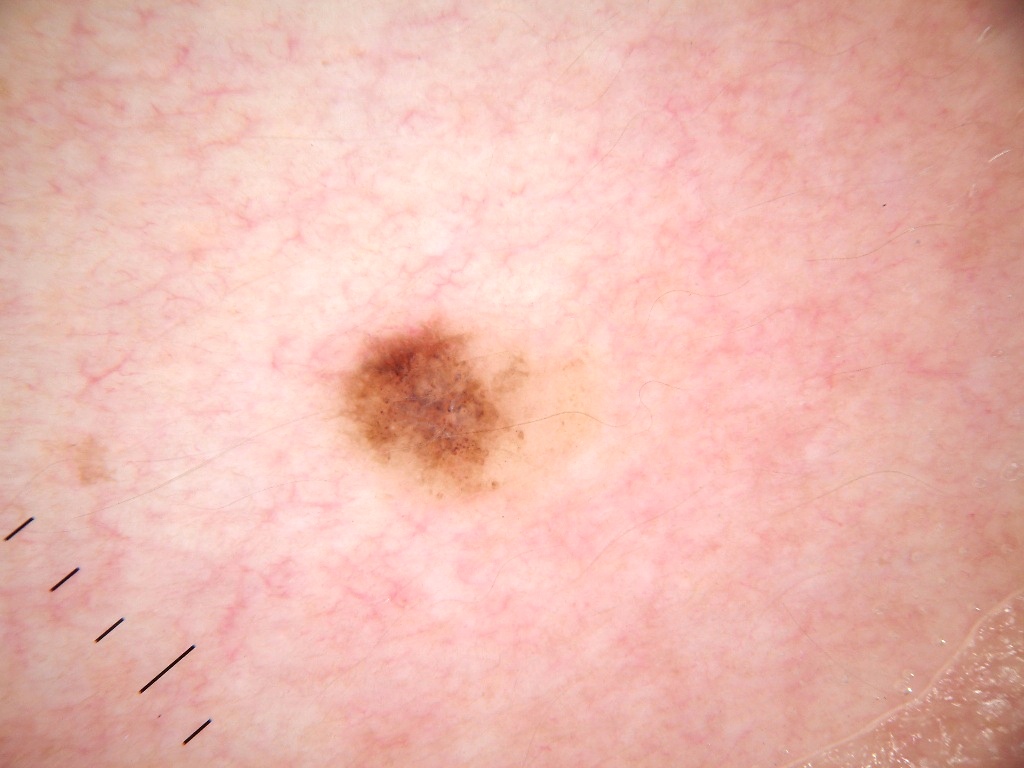Summary:
Dermoscopy of a skin lesion. The dermoscopic pattern shows milia-like cysts; no negative network, globules, streaks, or pigment network. The lesion takes up about 5% of the image. The lesion is bounded by 315, 309, 599, 507.
Impression:
Diagnosed as a melanocytic nevus.